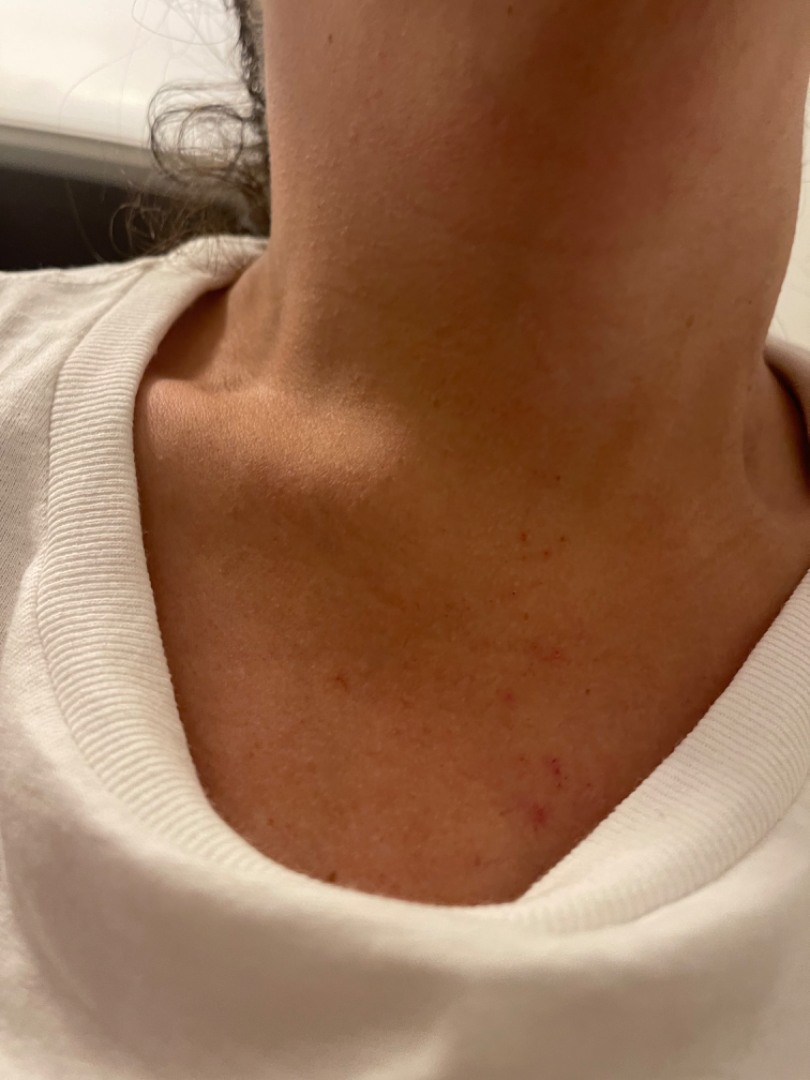The skin condition could not be confidently assessed from this image.